The contributor is a female aged 18–29, close-up view — 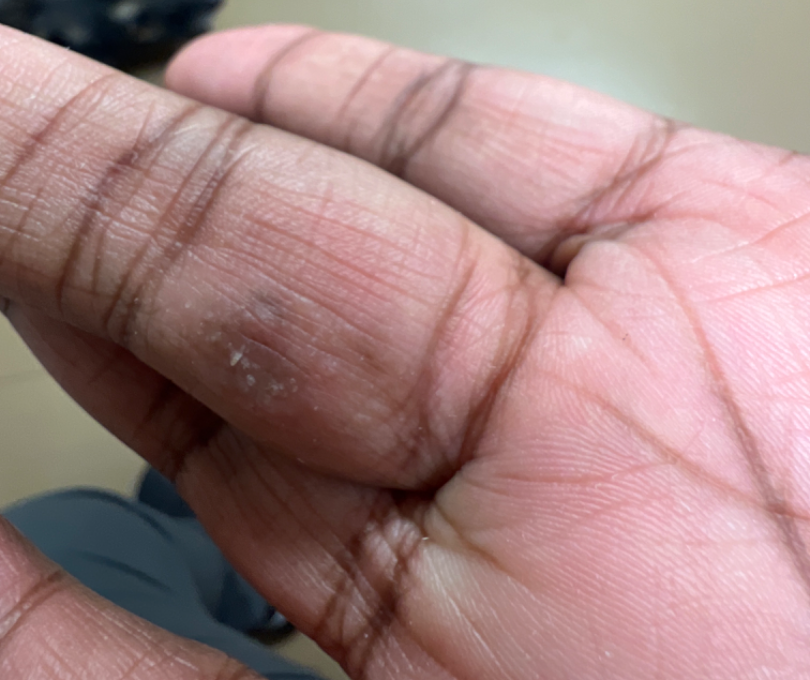Most consistent with Verruca vulgaris.